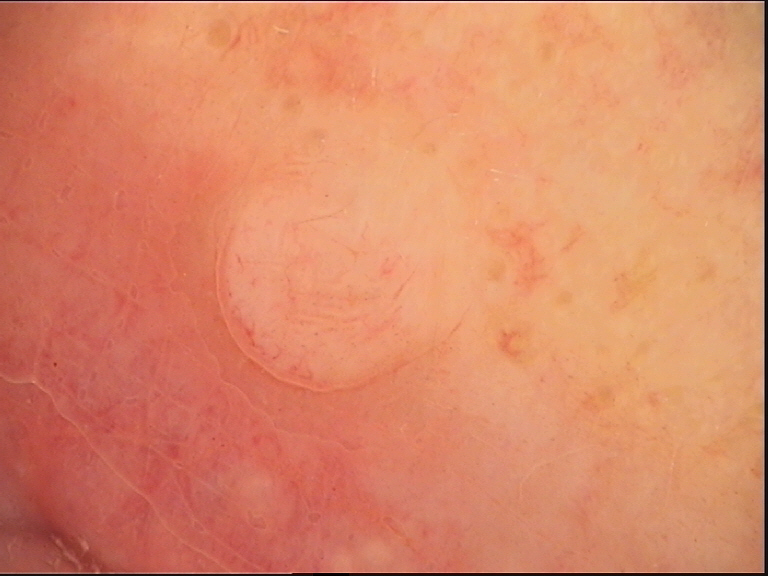{"image": "dermoscopy", "lesion_type": {"main_class": "banal", "pattern": "dermal"}, "diagnosis": {"name": "dermal nevus", "code": "db", "malignancy": "benign", "super_class": "melanocytic", "confirmation": "expert consensus"}}